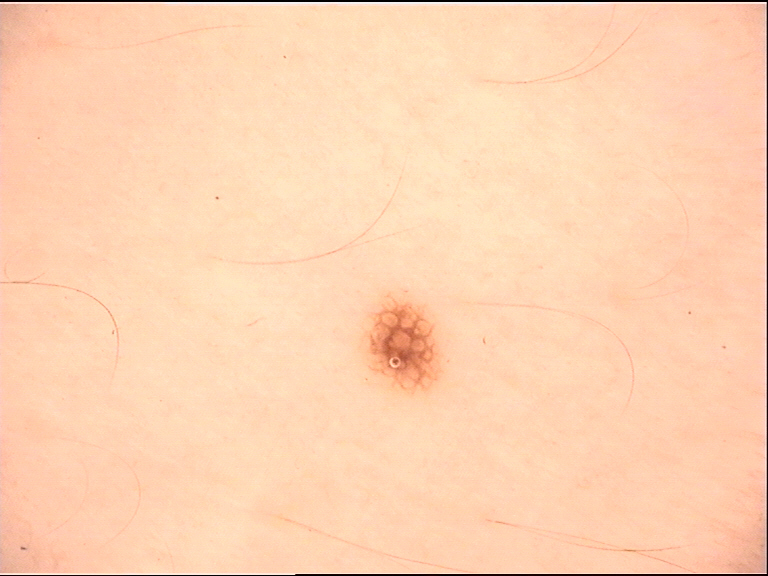label: dysplastic junctional nevus (expert consensus).